History notes prior skin cancer (patient or family). The patient is Fitzpatrick phototype III. A clinical close-up photograph of a skin lesion. A male subject 55 years old:
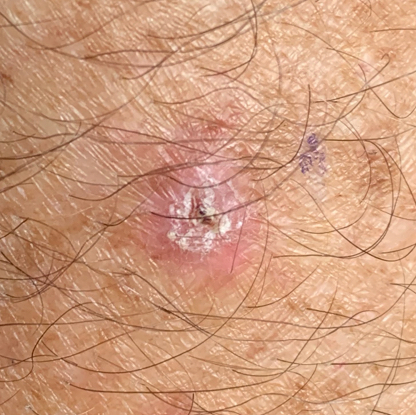Clinical context:
The lesion is located on a forearm.
Conclusion:
The biopsy diagnosis was a lesion with uncertain malignant potential — an actinic keratosis.